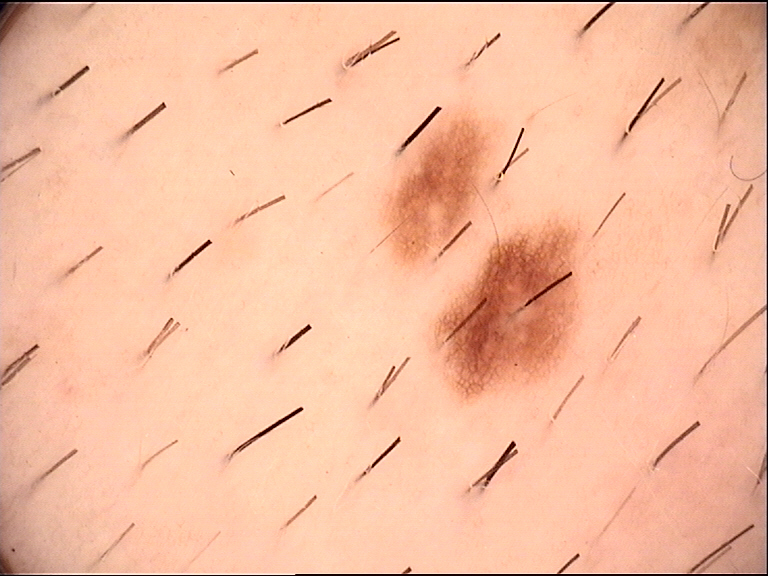The diagnosis was a dysplastic junctional nevus.